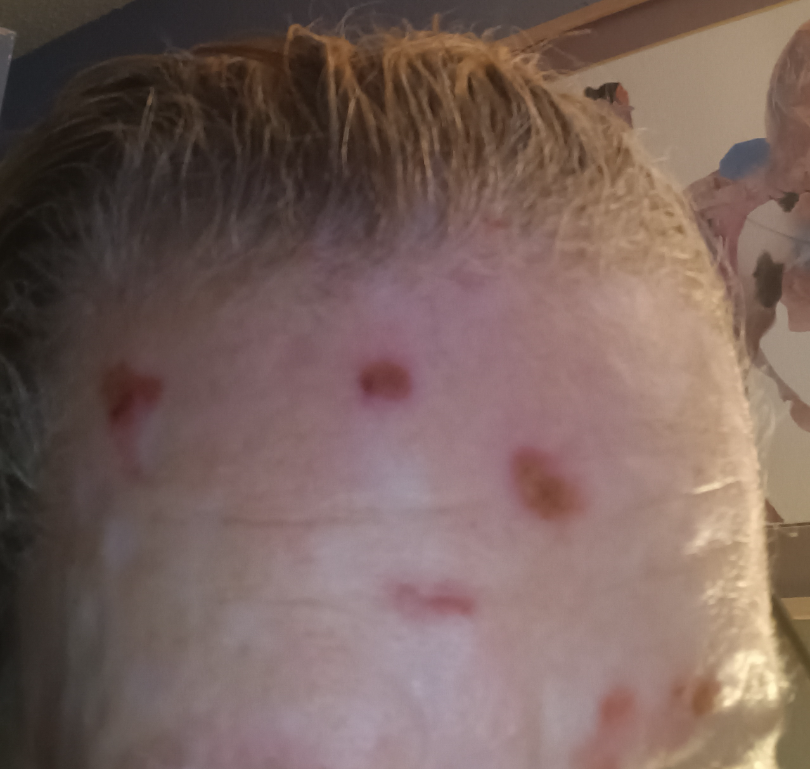Female subject, age 50–59. Located on the head or neck, top or side of the foot, arm, leg and front of the torso. Associated systemic symptoms include fatigue and fever. Reported duration is one to three months. The lesion is described as rough or flaky, fluid-filled and raised or bumpy. The lesion is associated with pain, bleeding, burning, bothersome appearance, itching and enlargement. Close-up view. The patient considered this a rash. Three dermatologists each reviewed the case: the leading consideration is Acne; possibly Inflicted skin lesions; lower on the differential is Impetigo; less probable is Lichen Simplex Chronicus; less likely is Herpes Zoster.